A dermoscopy image of a single skin lesion:
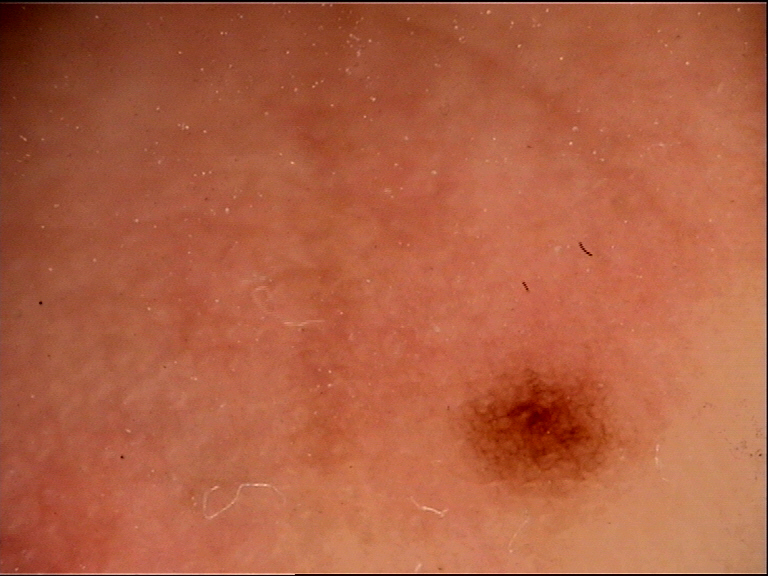assessment: acral junctional nevus (expert consensus).